The patient reports a personal history of skin cancer and a personal history of cancer. A female subject age 60. Few moles overall by the patient's own estimate. The referring clinician suspected basal cell carcinoma. A dermoscopic image of a skin lesion.
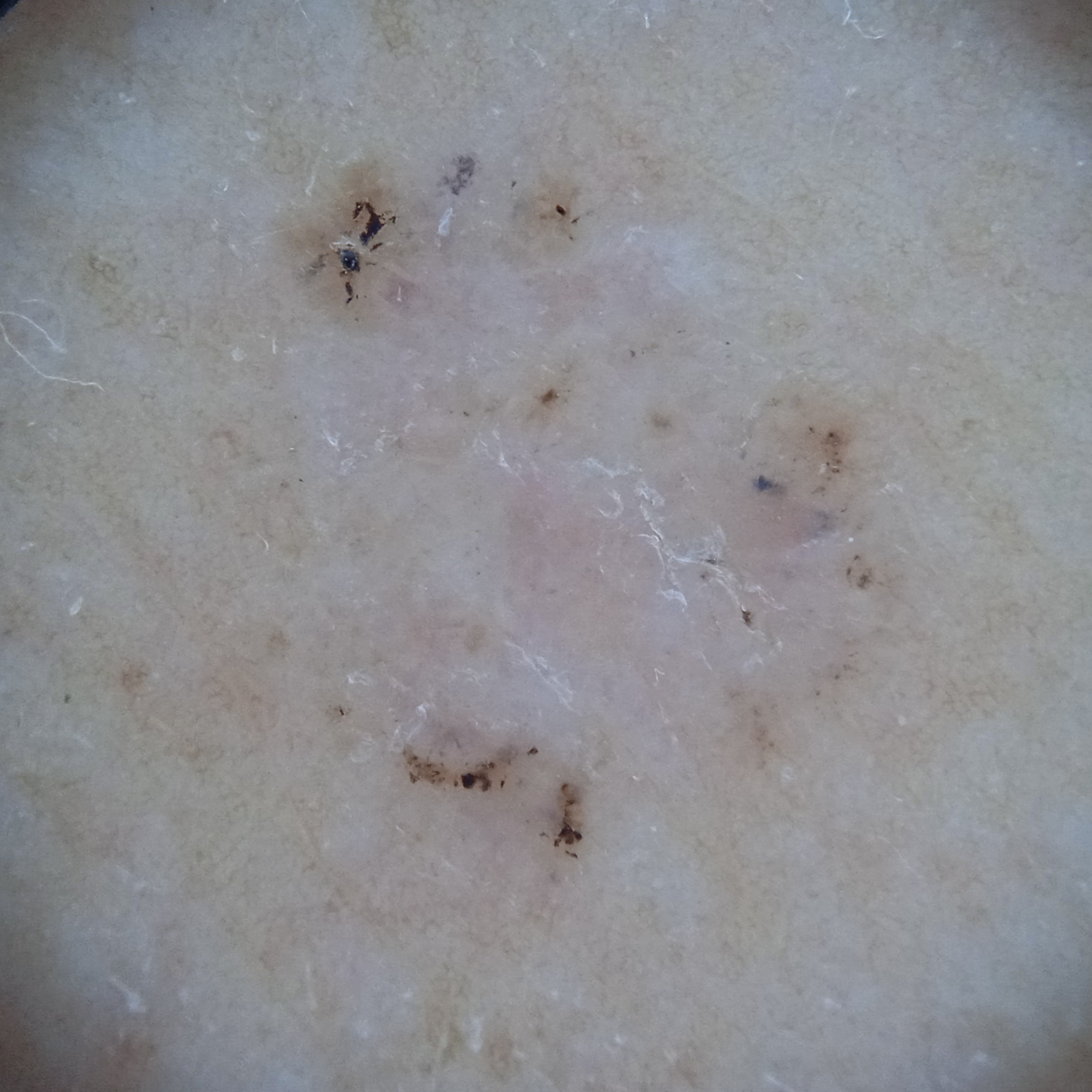Q: Where is the lesion?
A: the back
Q: How large is the lesion?
A: 7.8 mm
Q: What was the diagnosis?
A: basal cell carcinoma (dermatologist consensus)